Dermoscopy of a skin lesion.
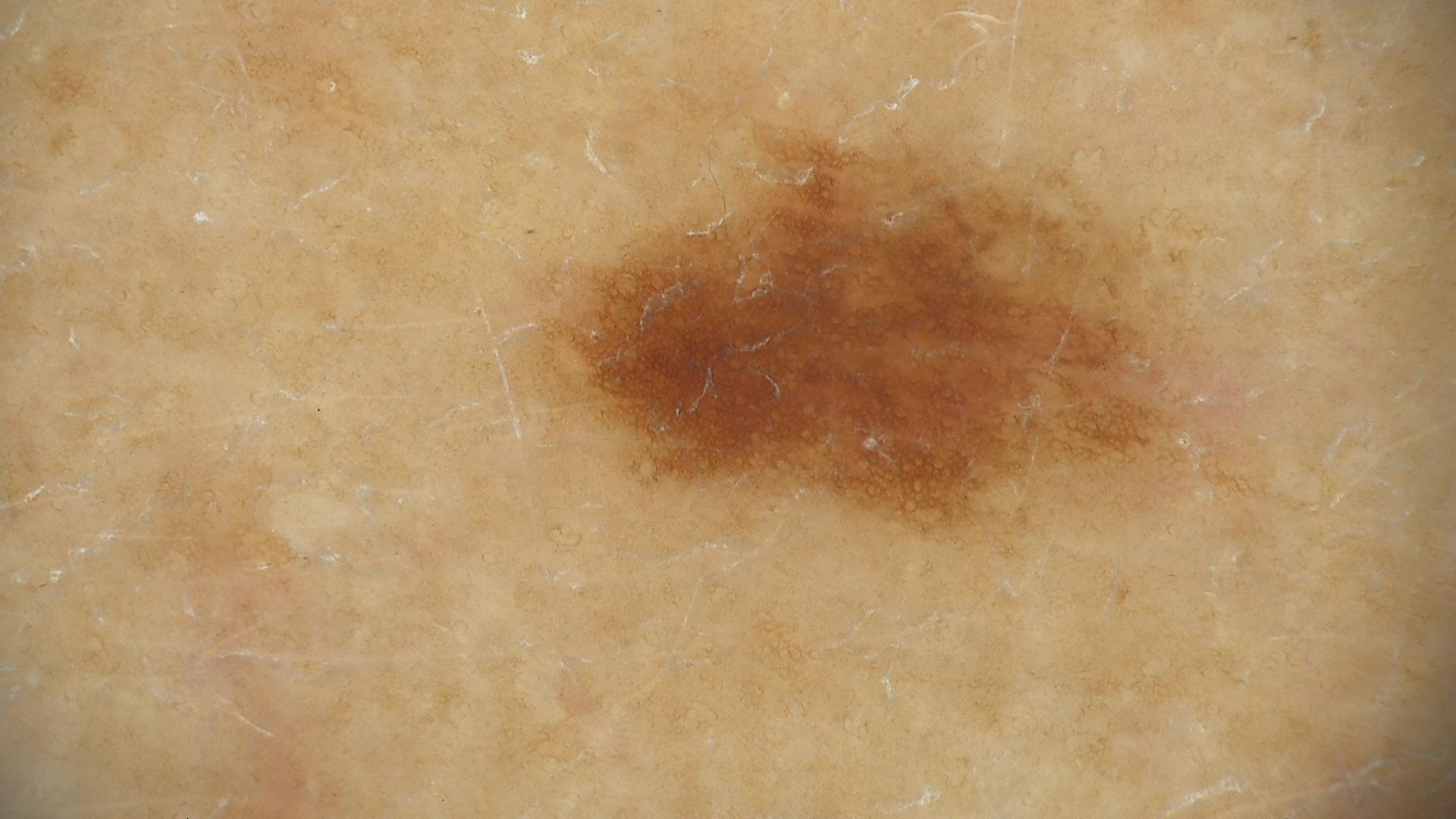Labeled as a benign lesion — a dysplastic junctional nevus.